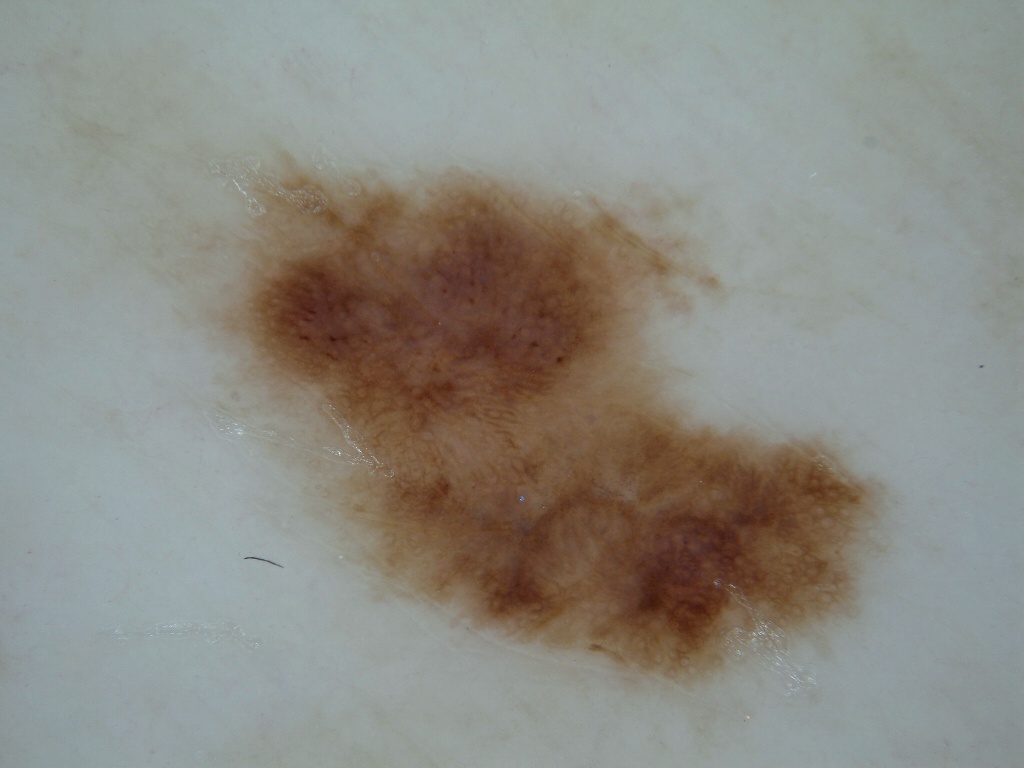Summary: Dermoscopy of a skin lesion. As (left, top, right, bottom), the lesion is located at (152, 143, 892, 731). Impression: The diagnostic assessment was a benign lesion.